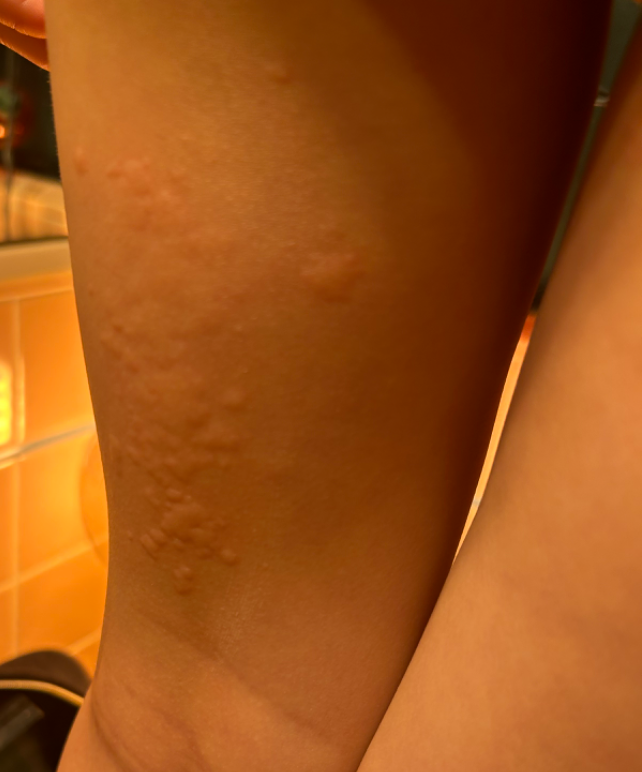lesion symptoms = itching, patient's own categorization = skin that appeared healthy to them, described texture = raised or bumpy, location = leg and front of the torso, onset = less than one week, framing = at a distance, dermatologist impression = the favored diagnosis is Urticaria; also on the differential is Allergic Contact Dermatitis; less likely is Insect Bite.